The photograph is a close-up of the affected area:
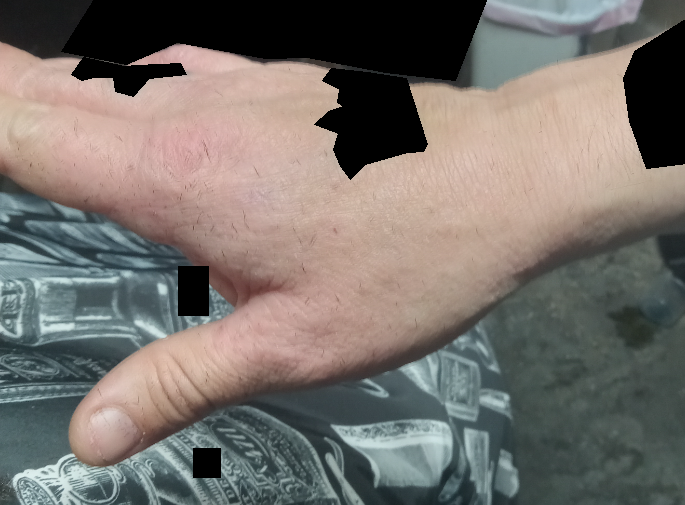The case was indeterminate on photographic review.